A male subject aged approximately 85 or older; Fitzpatrick skin type III; a dermoscopic image of a skin lesion: 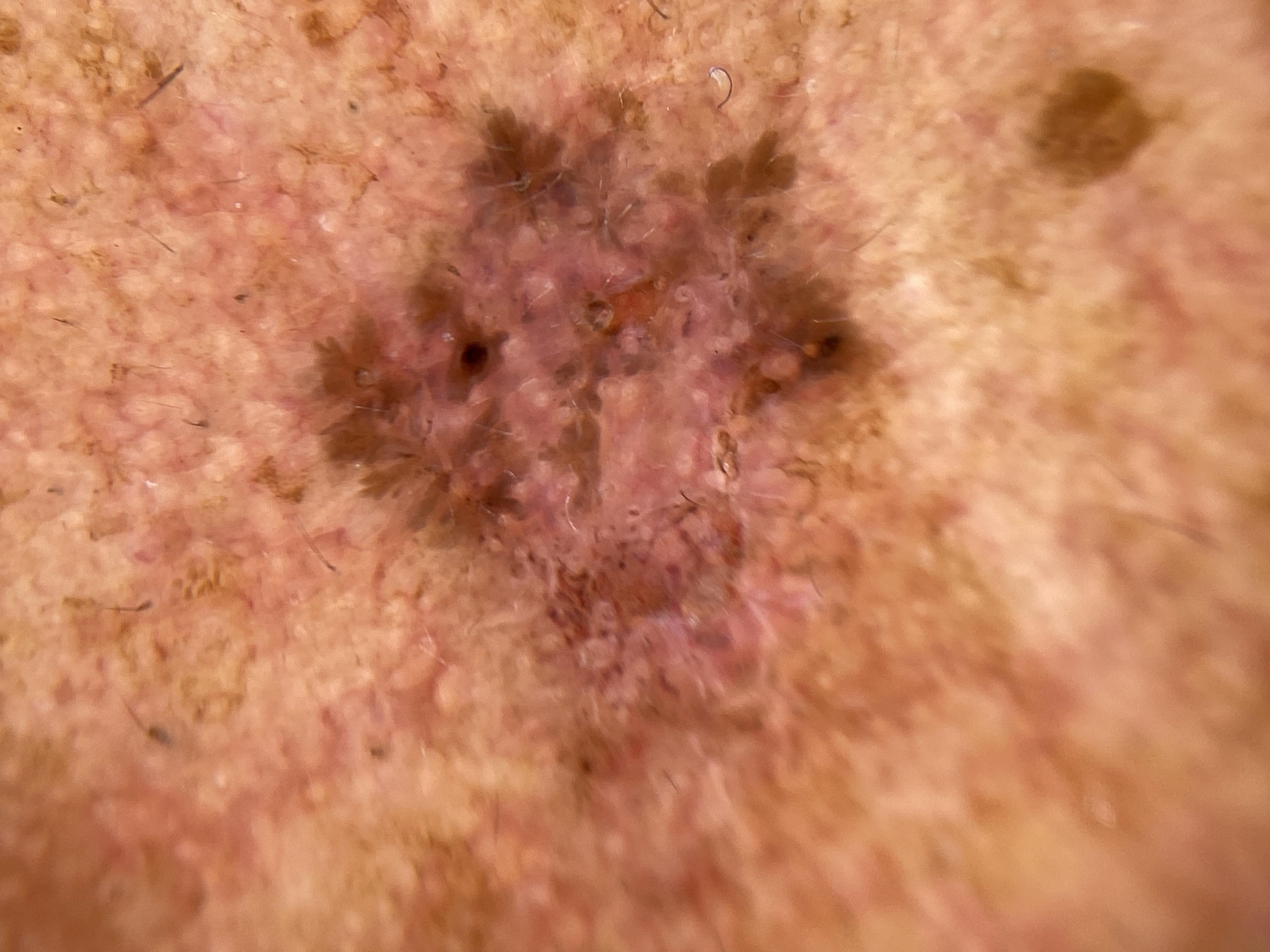The lesion was found on the head or neck.
Histopathology confirmed a basal cell carcinoma.